The arm, leg and front of the torso are involved; an image taken at an angle; the subject is a male aged 18–29.
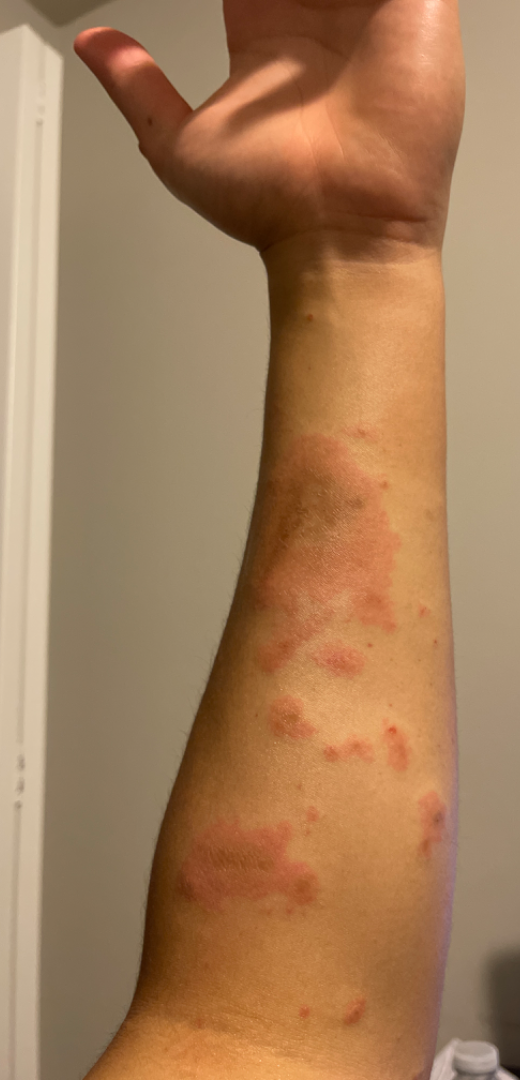Findings: Contact dermatitis and Erythema multiforme were considered with similar weight; also on the differential is Allergic Contact Dermatitis.